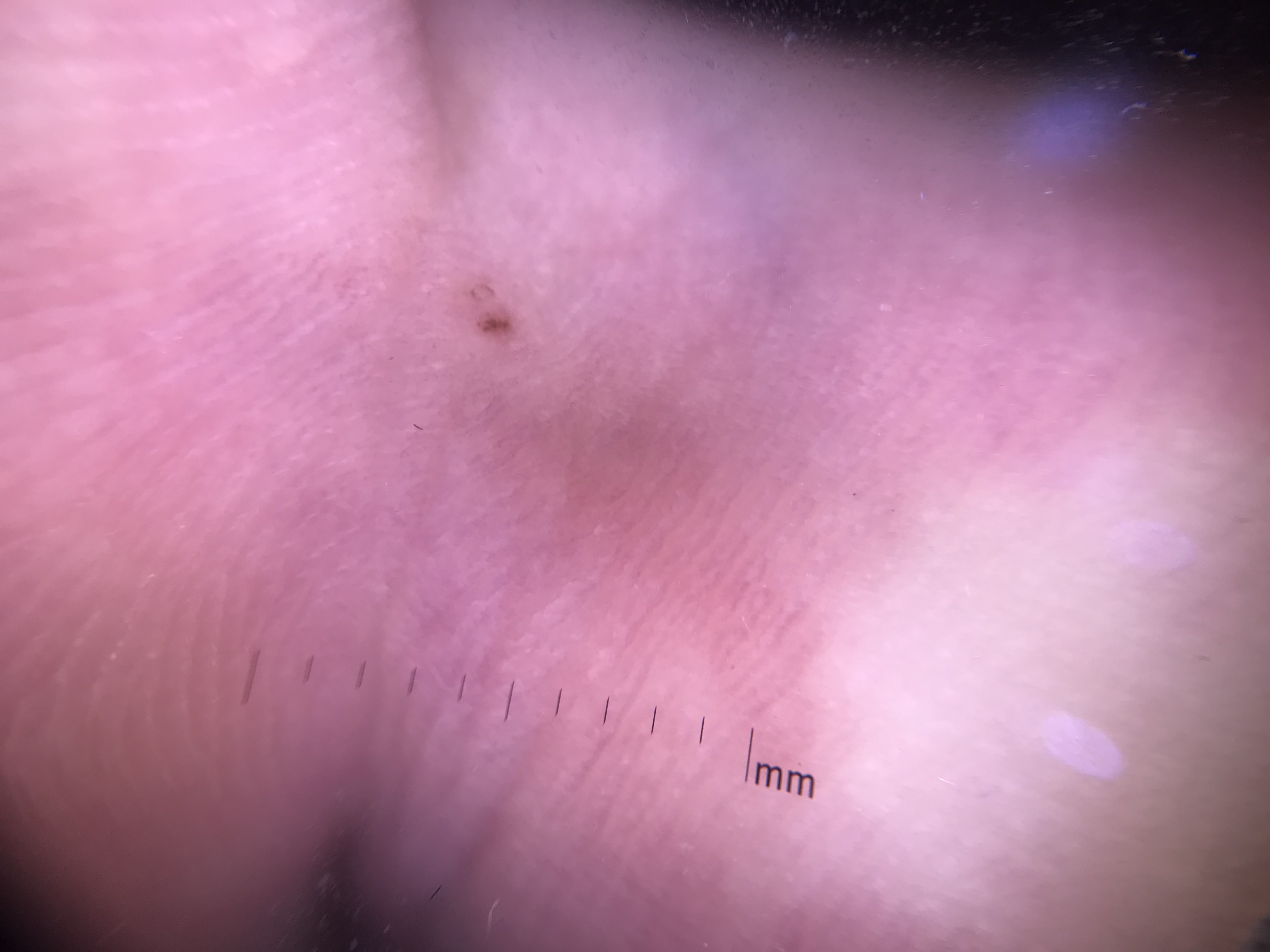image type — dermatoscopy | classification — banal | diagnosis — acral junctional nevus (expert consensus).